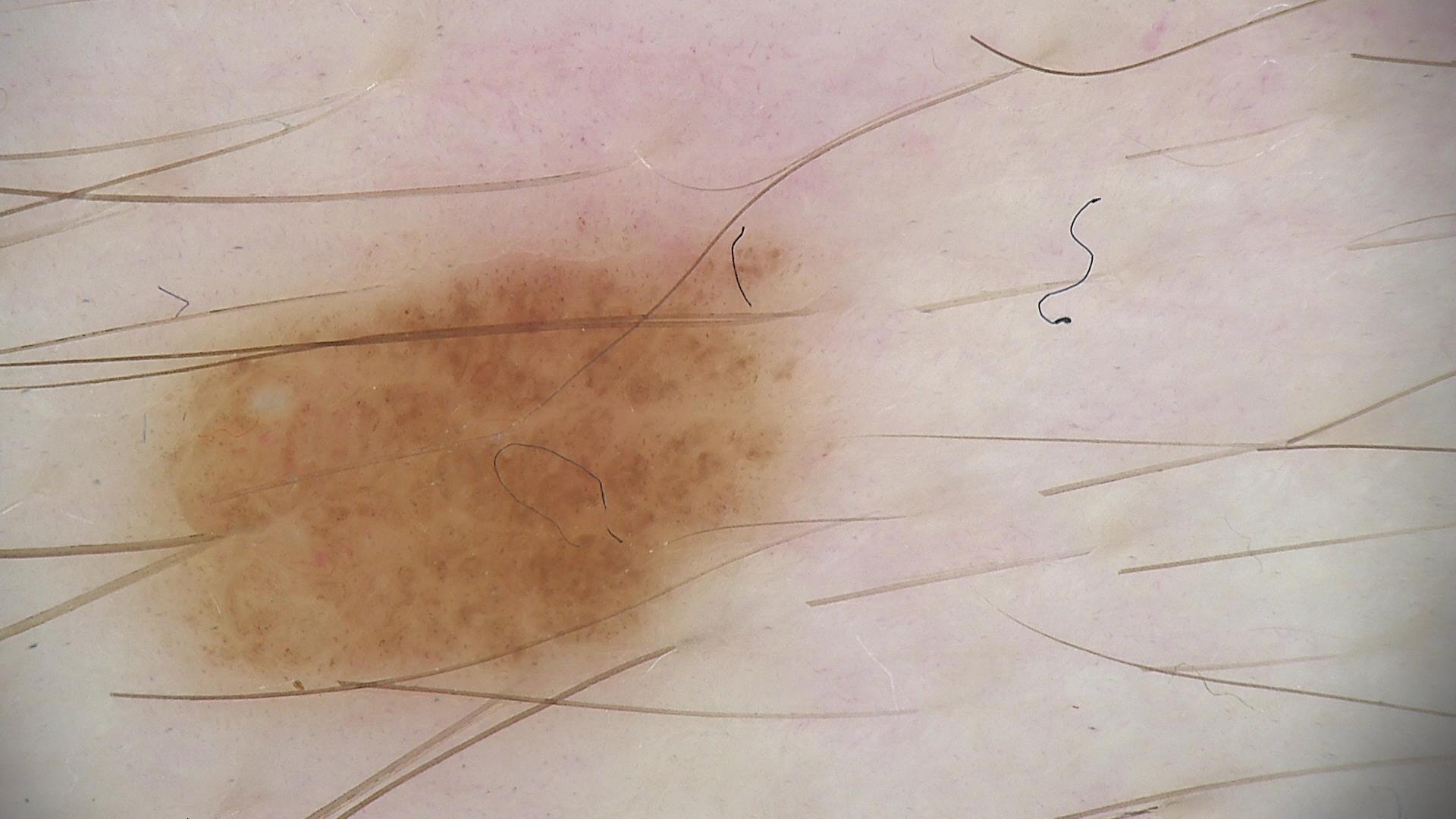Summary: A dermoscopy image of a single skin lesion. Conclusion: Labeled as a dysplastic junctional nevus.